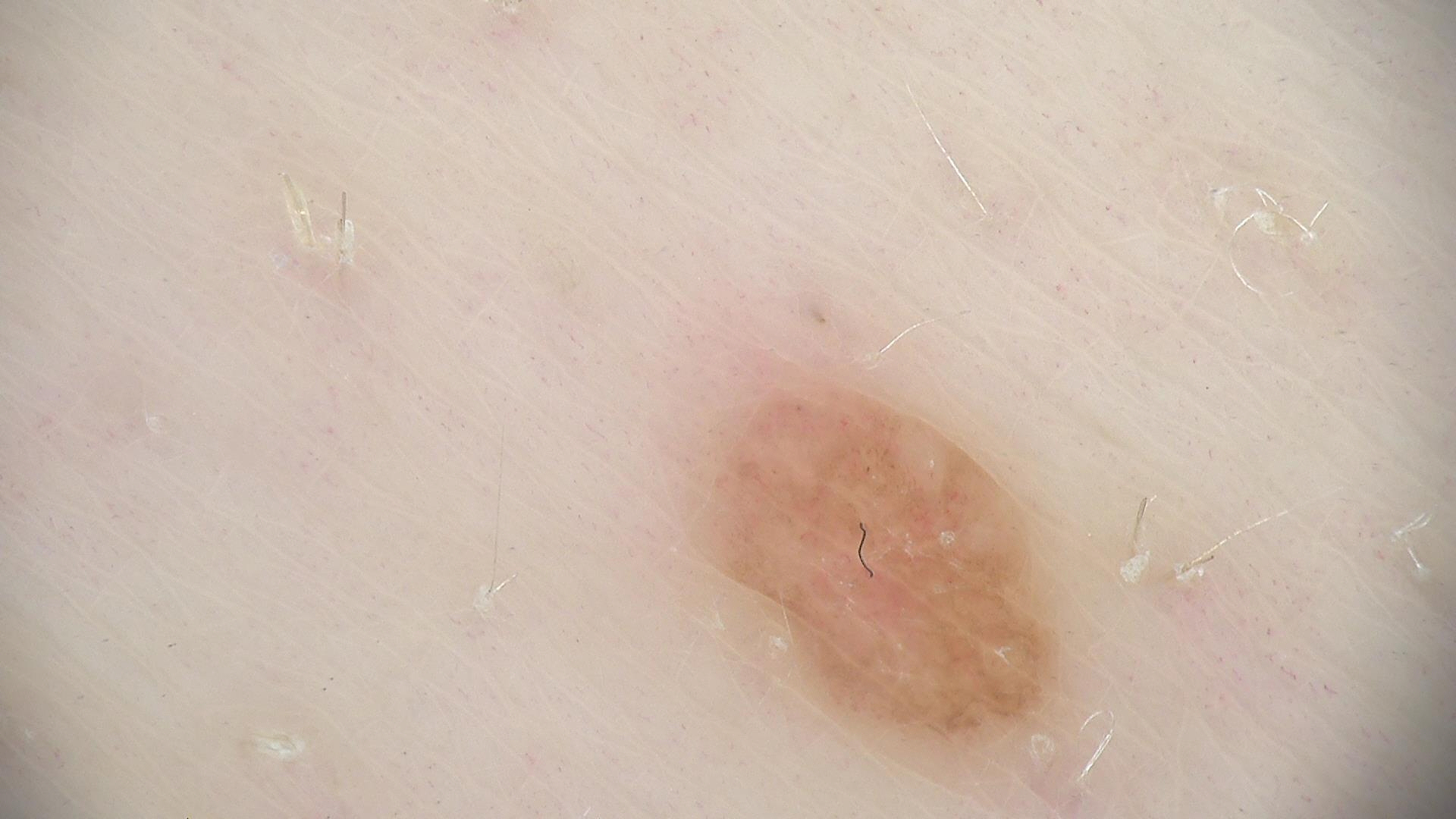The diagnosis was a dermal nevus.